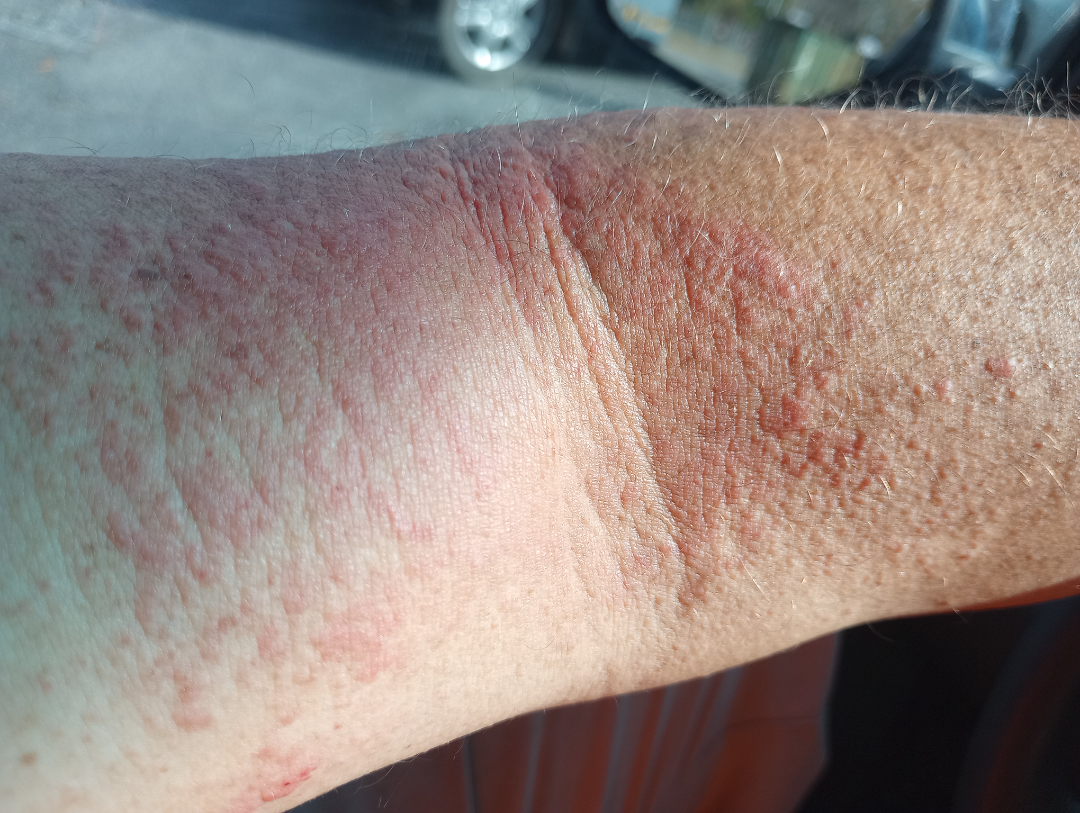Close-up view. Male contributor, age 40–49. Located on the arm. On remote dermatologist review, most likely Eczema; with consideration of Psoriasis; possibly Allergic Contact Dermatitis.